Fitzpatrick phototype III · a female subject approximately 50 years of age · a skin lesion imaged with contact-polarized dermoscopy.
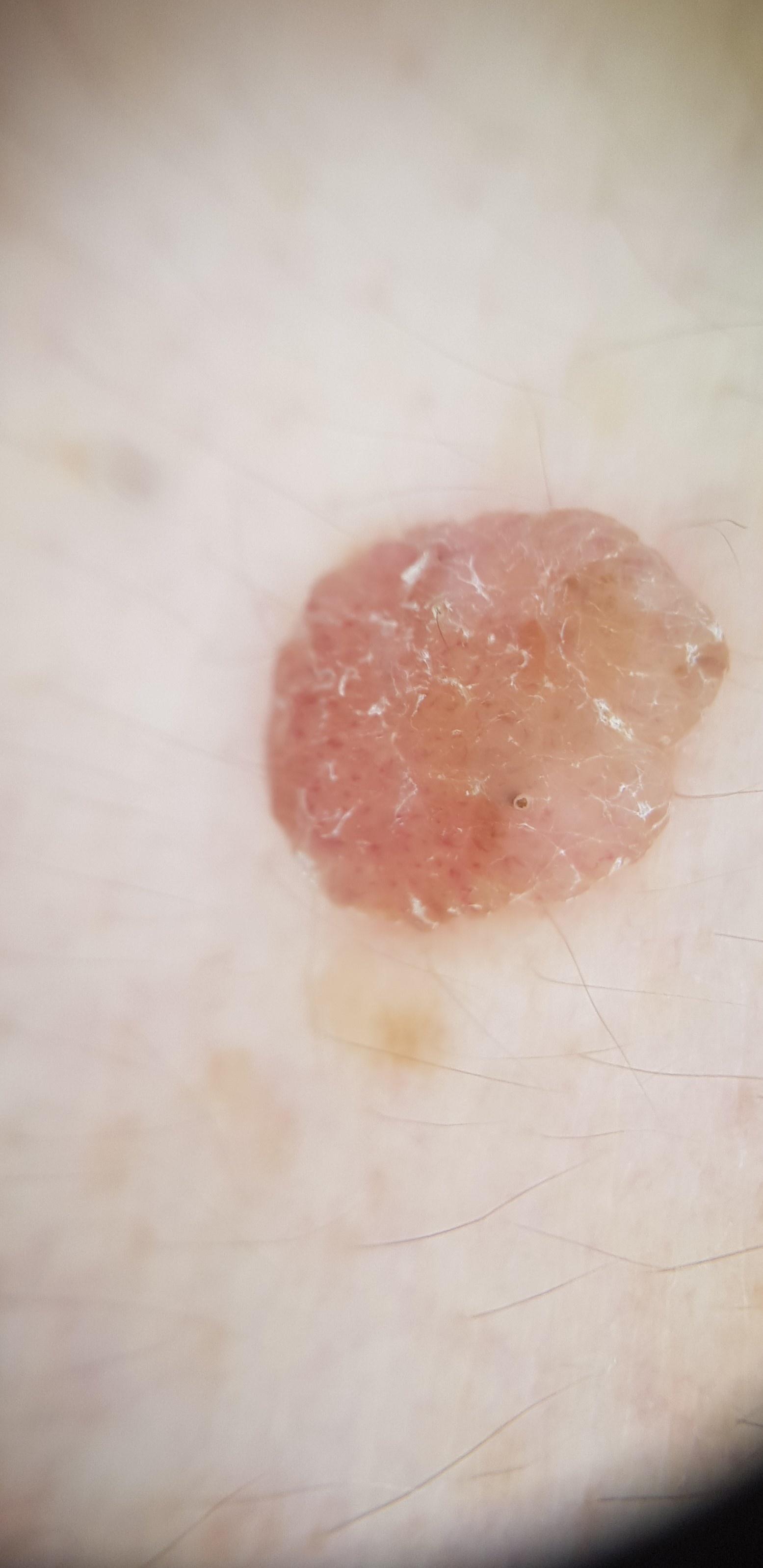The lesion involves the trunk. Histopathological examination showed a benign lesion — a nevus.